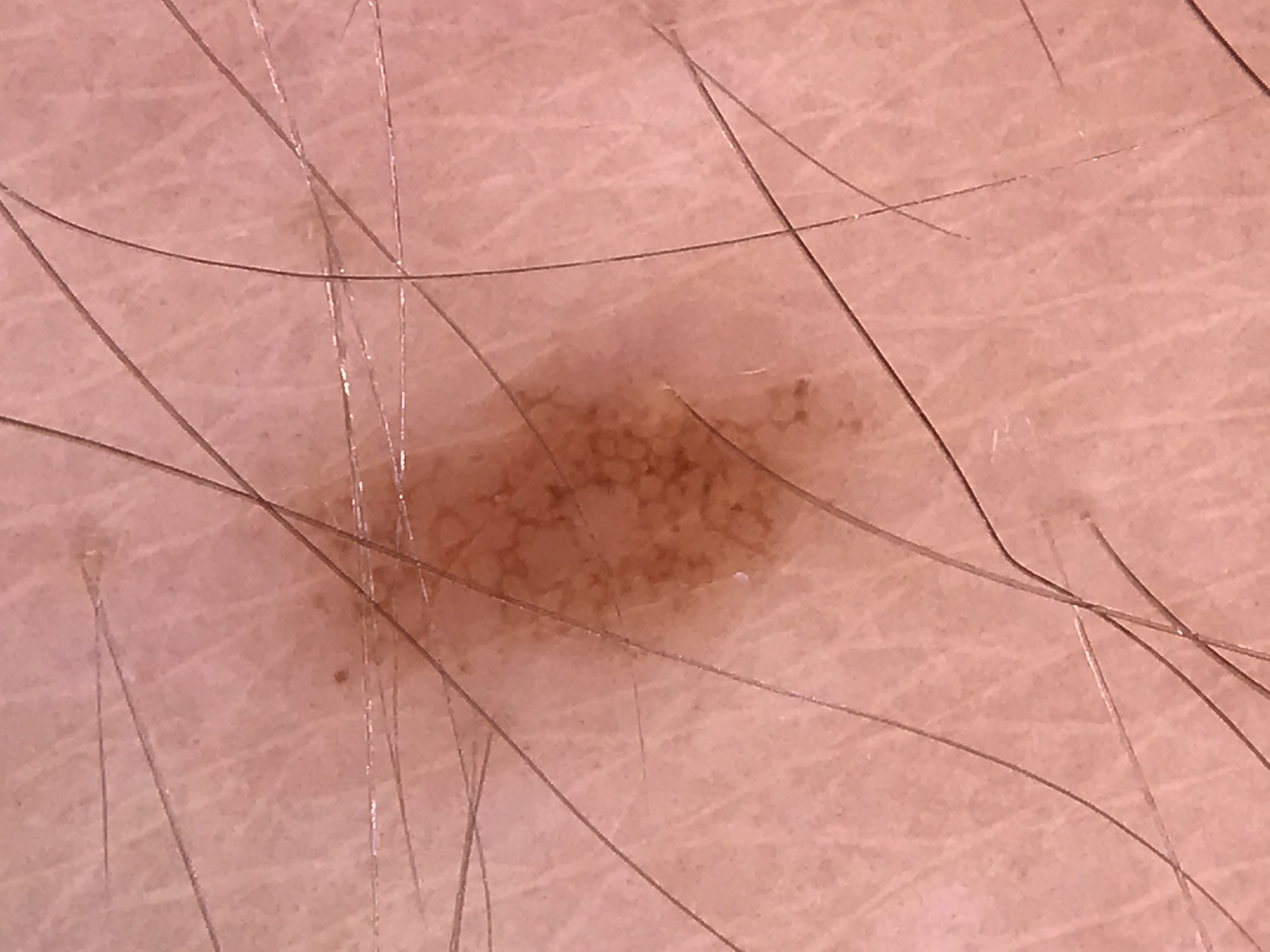diagnostic label: junctional nevus (expert consensus).